Reported duration is less than one week. The contributor is 18–29, female. Fitzpatrick I; lay graders estimated MST 2 or 3 (two reviewer pools). The patient reported no systemic symptoms. The contributor reports the lesion is raised or bumpy. The patient described the issue as skin that appeared healthy to them. This image was taken at a distance. Located on the arm. The contributor reports itching:
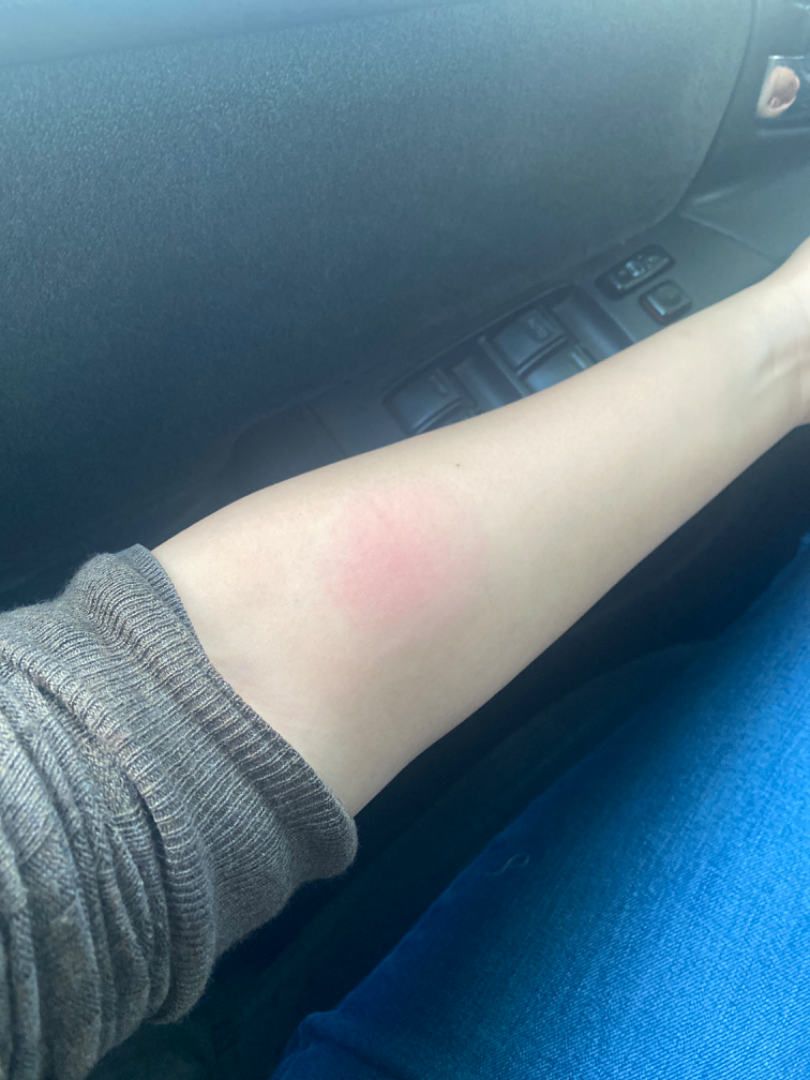  differential:
    leading:
      - Insect Bite
    considered:
      - Erythema annulare centrifugum